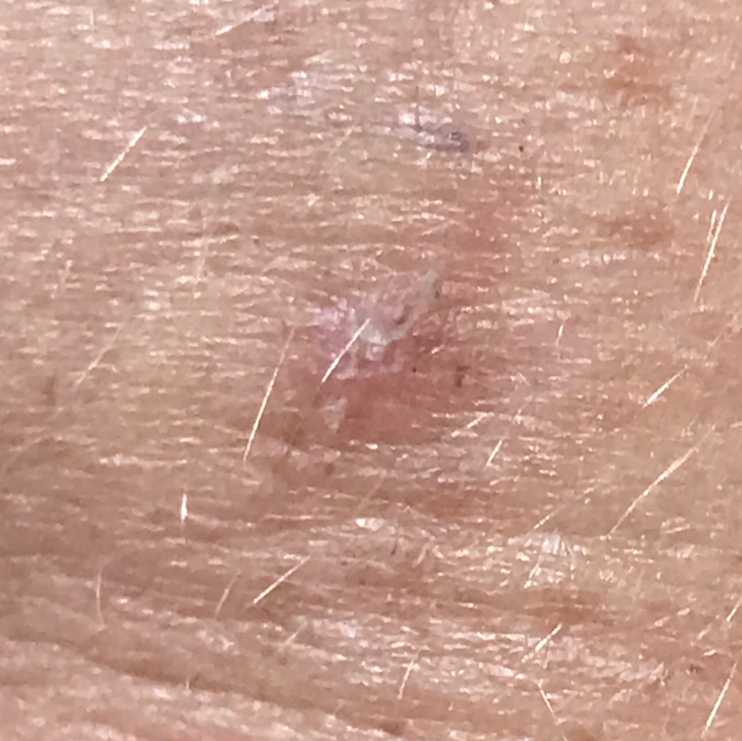imaging: clinical photograph | patient: age 42 | anatomic site: an arm | symptoms: itching, elevation | impression: actinic keratosis (clinical consensus).